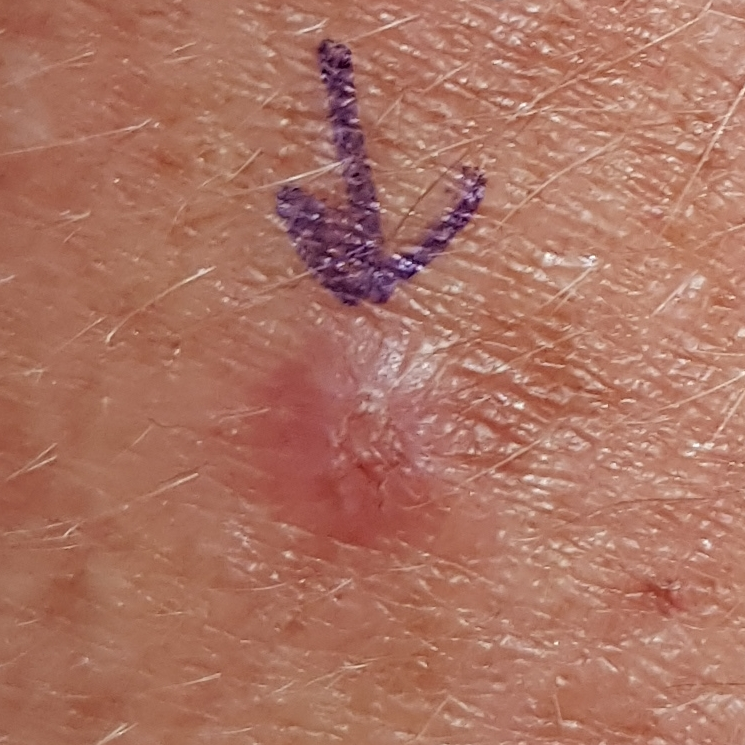patient=age 46
imaging=clinical photograph
region=a forearm
reported symptoms=itching, elevation, growth / no change in appearance
impression=actinic keratosis (clinical consensus)